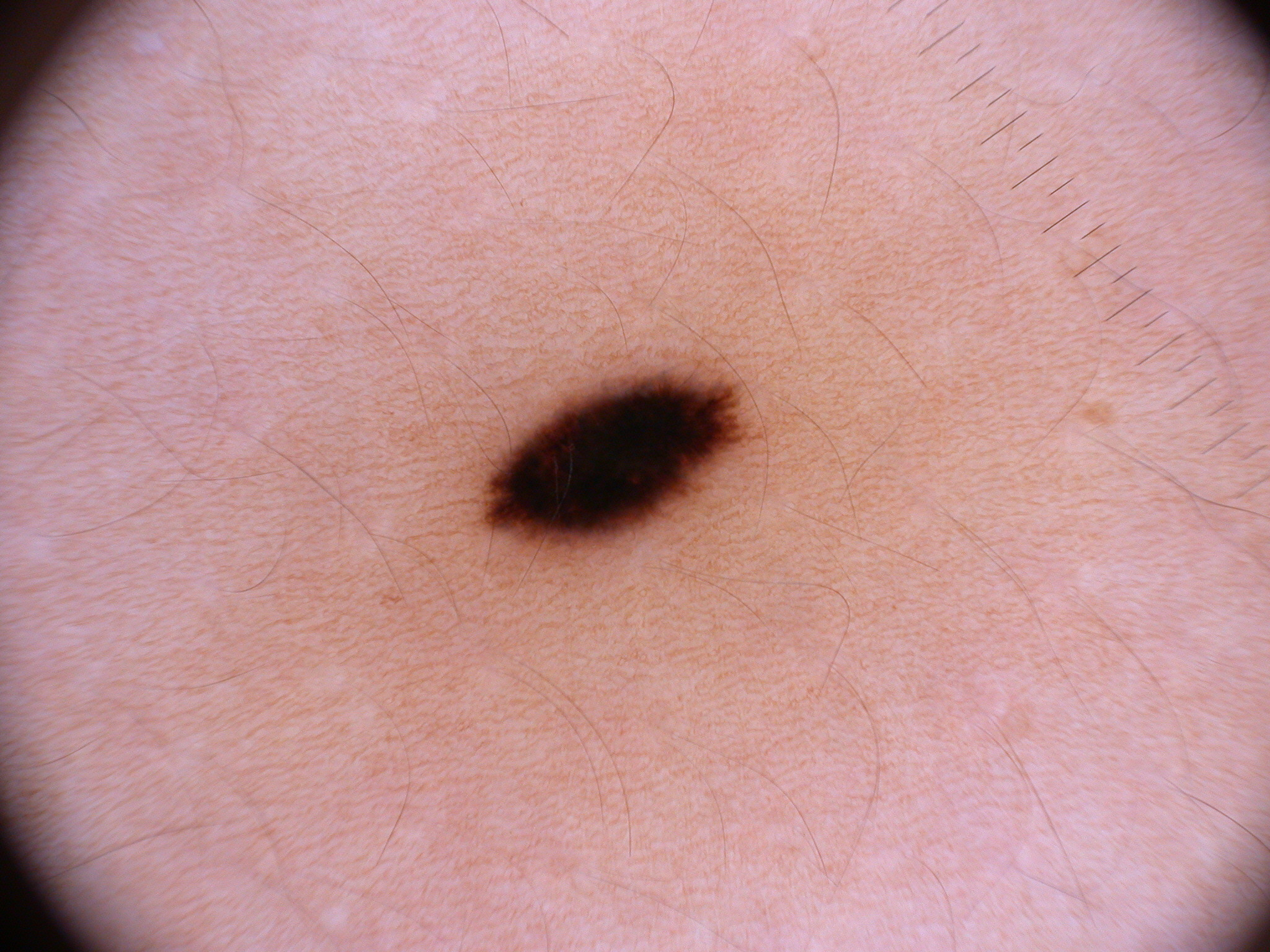Image and clinical context:
This is a dermoscopic photograph of a skin lesion. The dermoscopic pattern shows streaks. The lesion takes up about 2% of the image. The visible lesion spans bbox=[488, 378, 733, 541].
Impression:
The diagnostic assessment was a melanocytic nevus, a benign lesion.